The patient says their skin reddens with sun exposure · acquired for a research image collection, with no referral diagnosis · a male patient 77 years old · by self-report, a personal history of cancer and a personal history of skin cancer · a dermatoscopic image of a skin lesion:
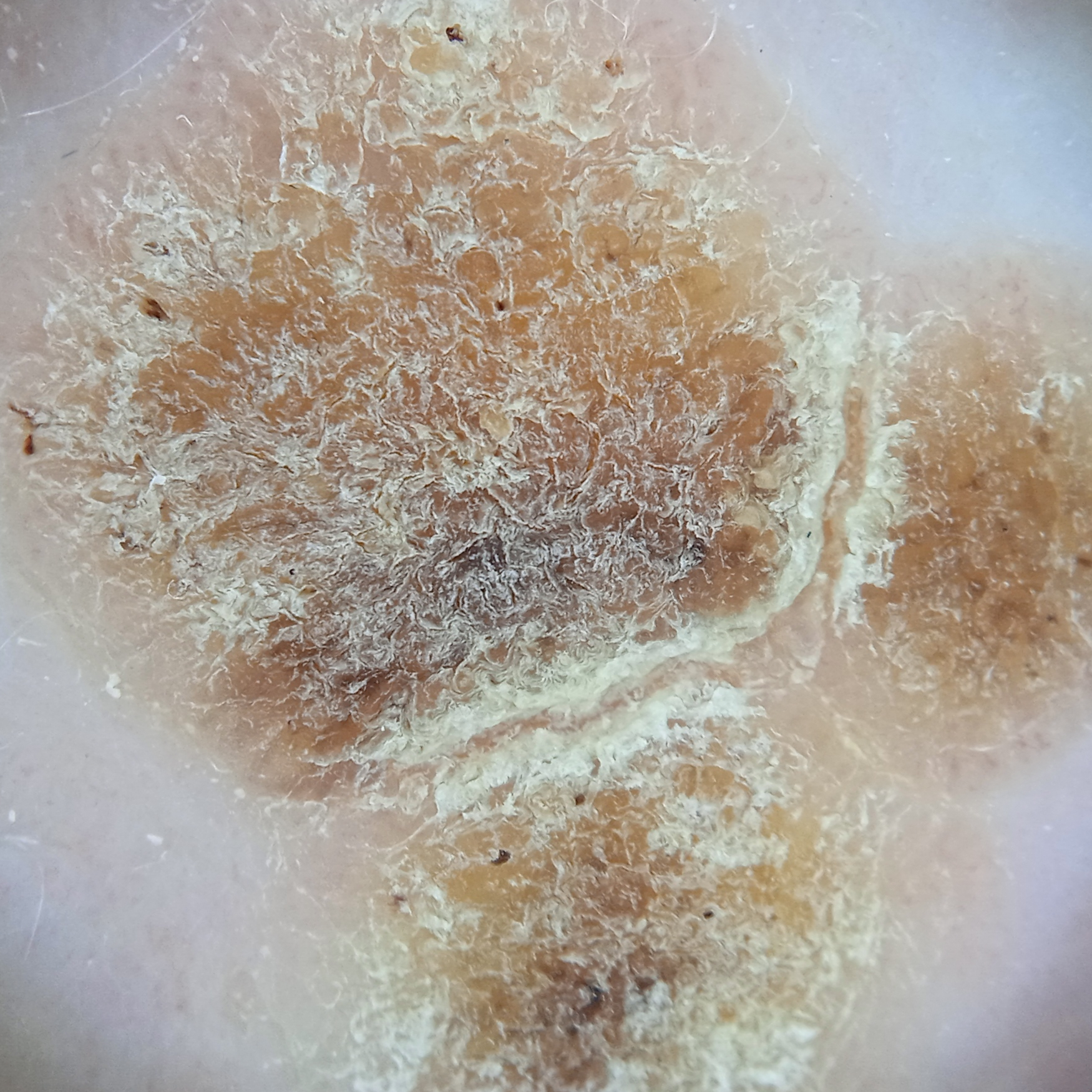The lesion measures approximately 14.2 mm.
The diagnostic impression was a seborrheic keratosis.